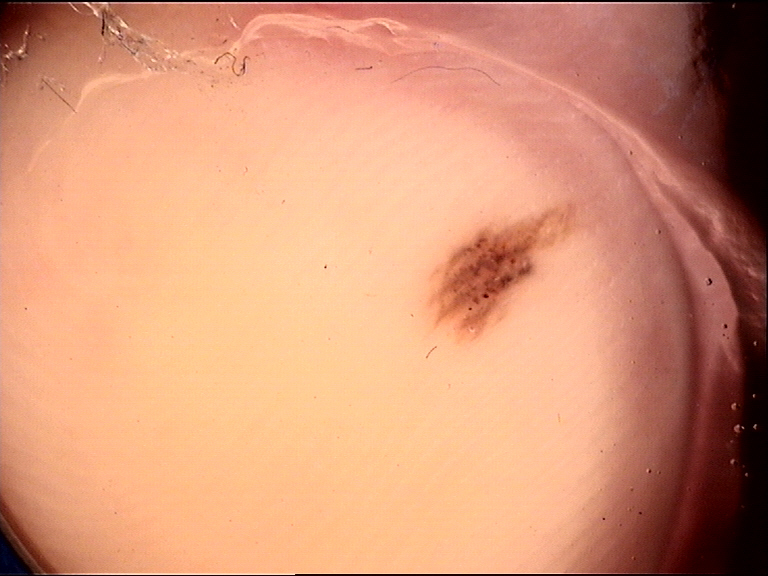Impression: Labeled as an acral dysplastic junctional nevus.